Imaged for a research study, with no referral diagnosis recorded. A male subject 83 years of age. A skin lesion imaged with a dermatoscope:
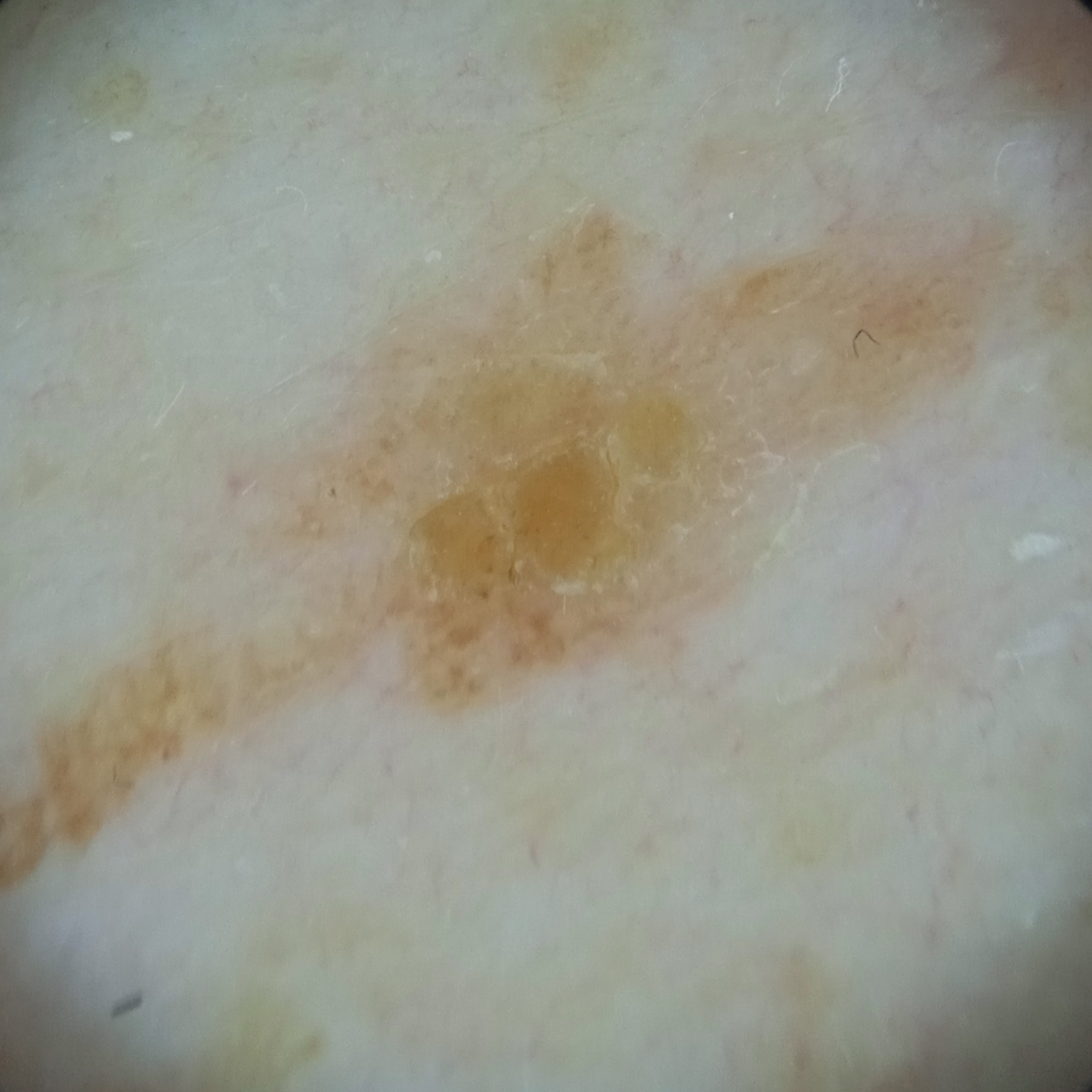anatomic site: the back
diameter: 16.4 mm
diagnosis: seborrheic keratosis (dermatologist consensus)